A skin lesion imaged with a dermatoscope:
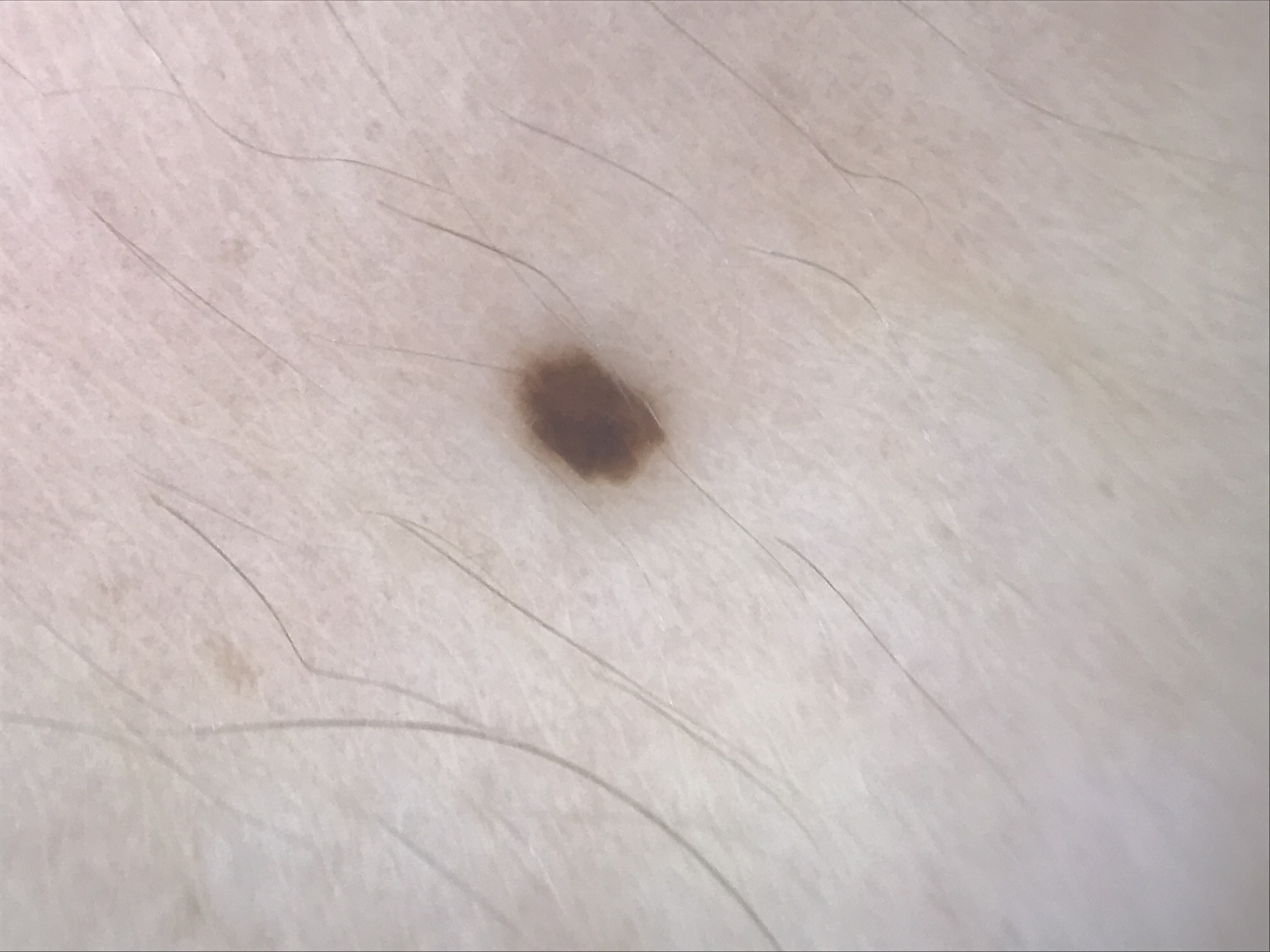Q: What is the lesion category?
A: banal
Q: What is the diagnosis?
A: junctional nevus (expert consensus)